A skin lesion imaged with a dermatoscope.
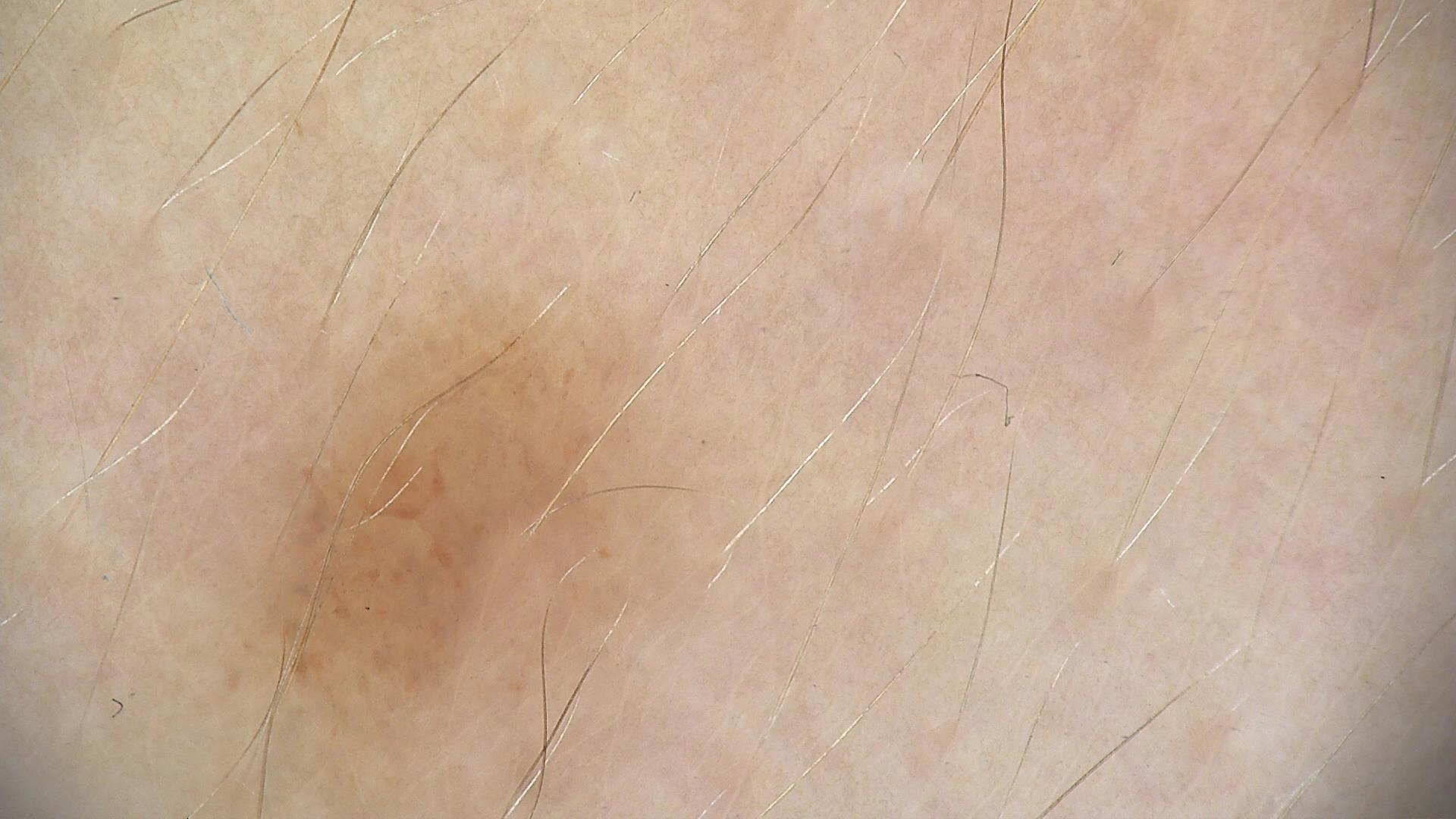  diagnosis:
    name: dysplastic junctional nevus
    code: jd
    malignancy: benign
    super_class: melanocytic
    confirmation: expert consensus